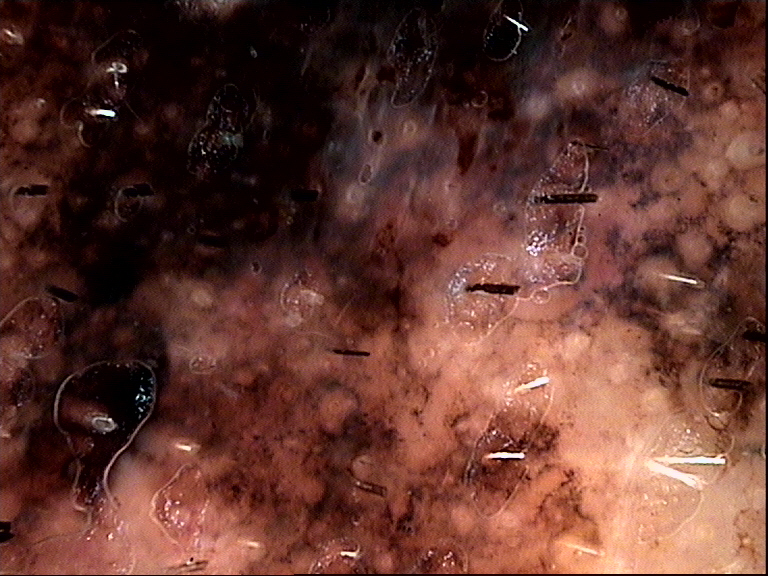diagnosis: lentigo maligna melanoma (biopsy-proven).